A dermatoscopic image of a skin lesion: 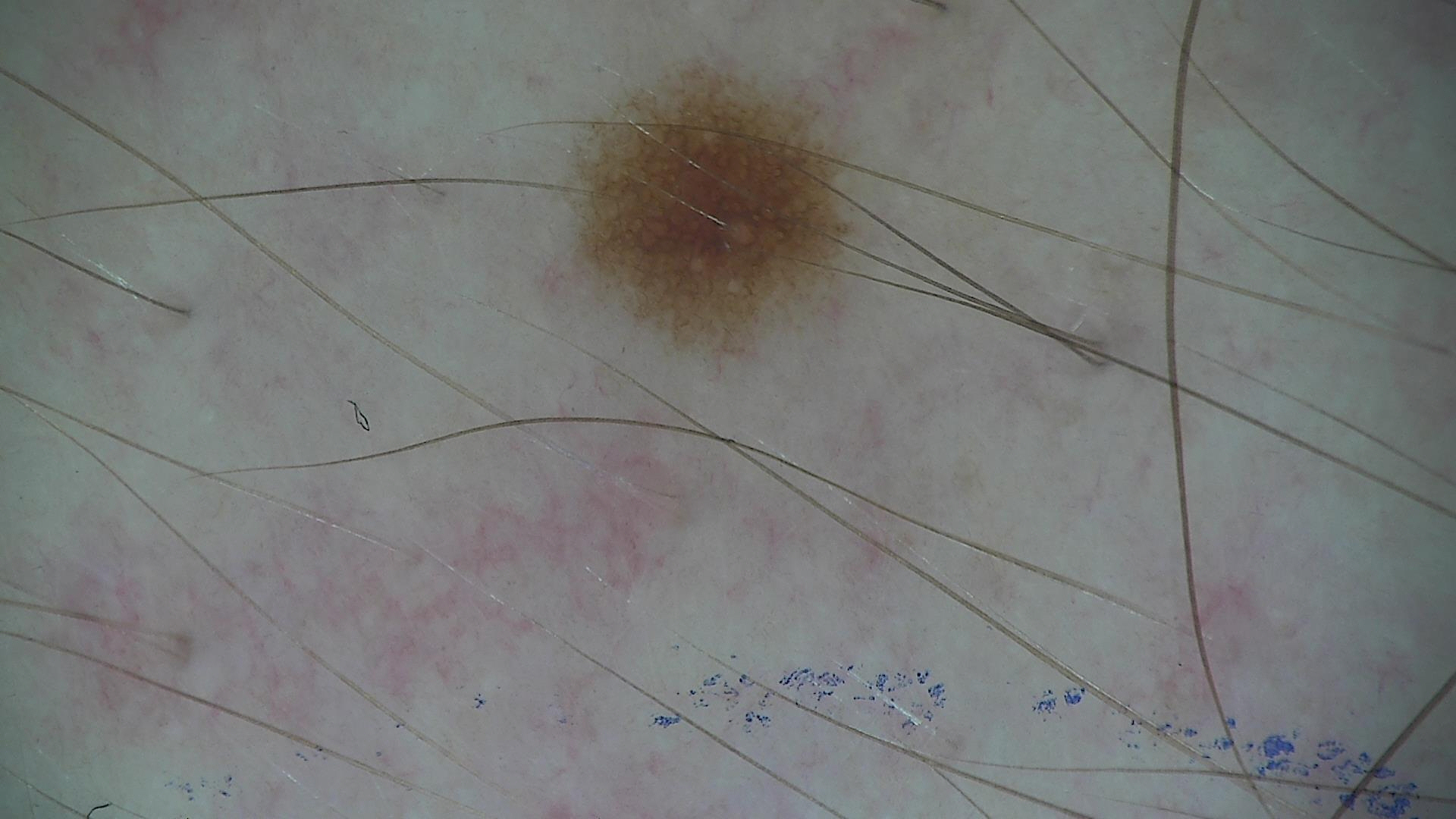The architecture is that of a banal lesion. Diagnosed as a junctional nevus.